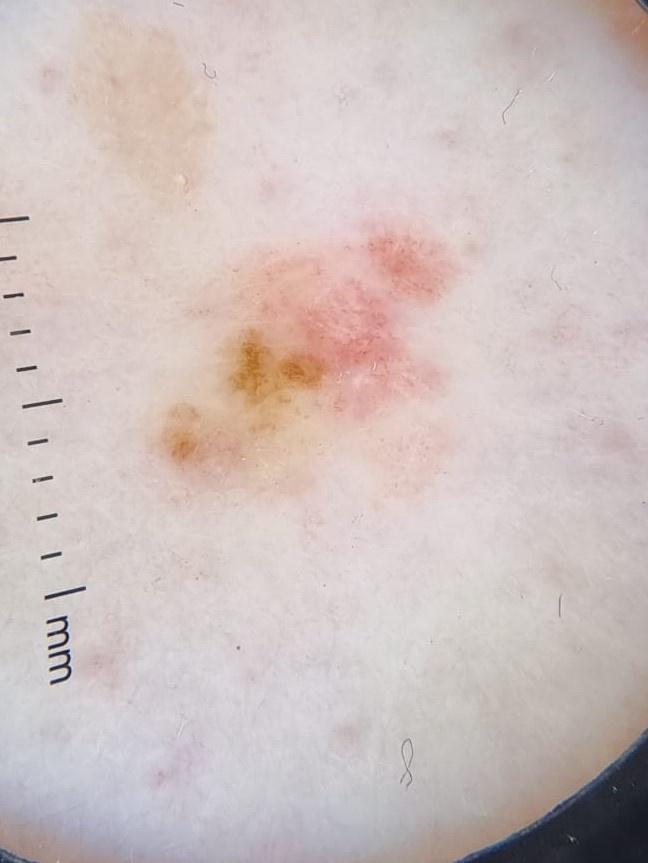patient=female, aged 63 to 67 | melanoma history=a prior melanoma | FST=I | modality=dermoscopic image | diagnosis=Melanoma (biopsy-proven).